This is a close-up image — 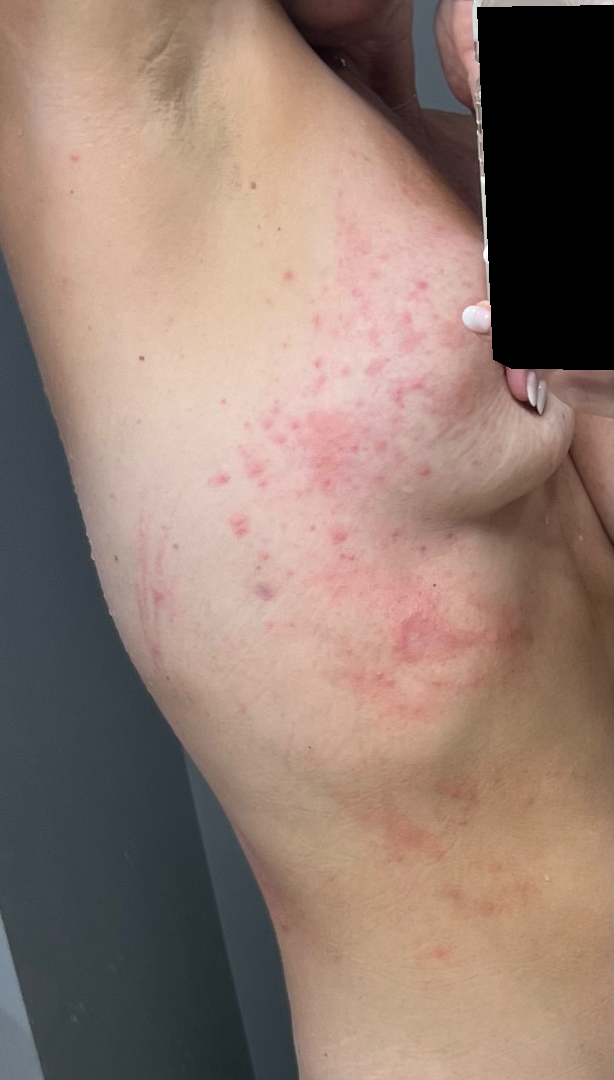The skin condition could not be confidently assessed from this image.